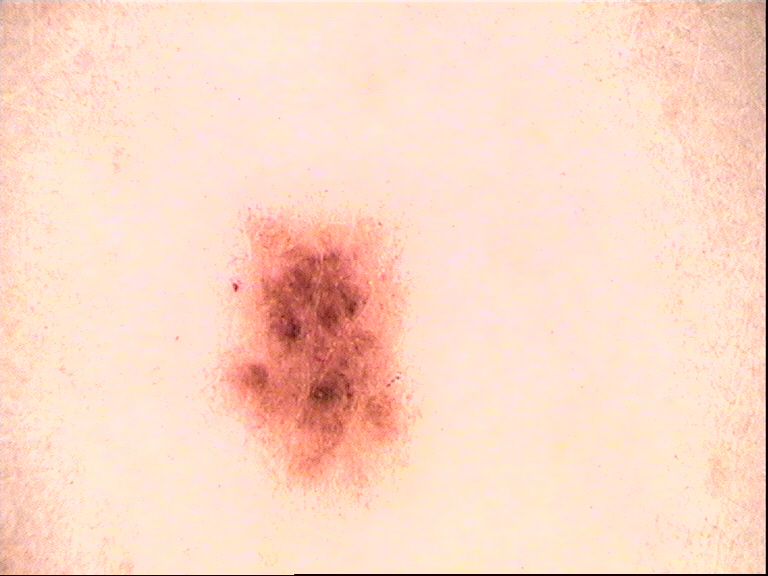image: dermoscopy
diagnosis:
  name: dysplastic junctional nevus
  code: jd
  malignancy: benign
  super_class: melanocytic
  confirmation: expert consensus